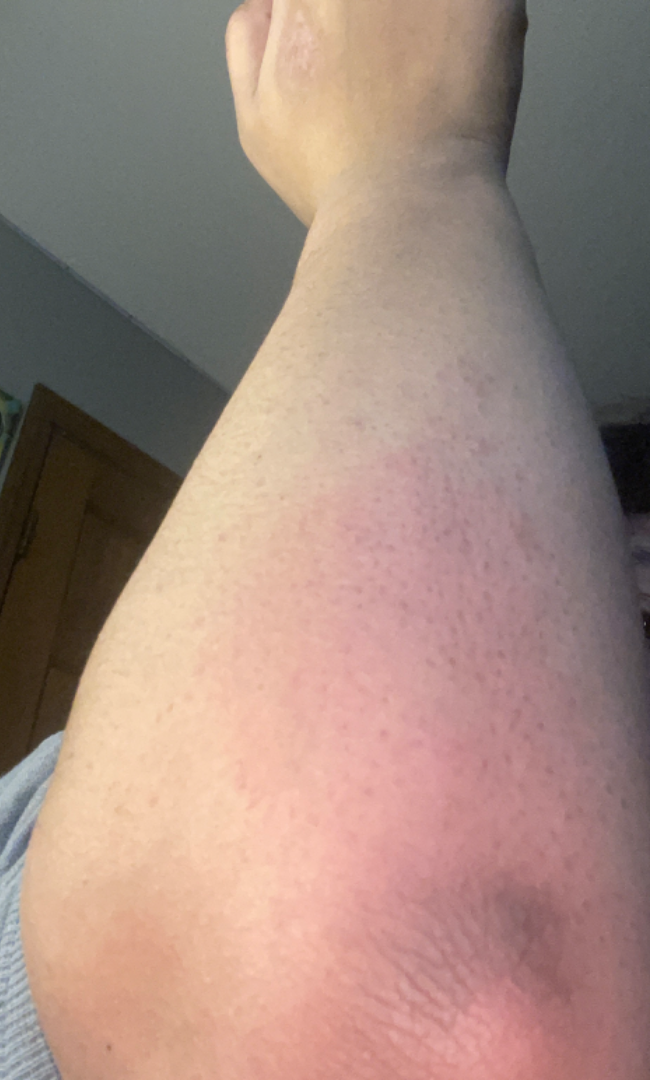Clinical context: The photo was captured at an angle. Skin tone: non-clinician graders estimated Monk skin tone scale 3 or 4 (two reviewer pools). Self-categorized by the patient as a rash. The patient indicates the condition has been present for about one day. The affected area is the front of the torso, leg, arm, back of the torso, head or neck and palm. The patient indicates enlargement and bothersome appearance. The patient indicates the lesion is flat. The patient is female. Assessment: On photographic review by a dermatologist: Urticaria (weight 1.00).